A male subject age 72; the patient is Fitzpatrick phototype II; the chart notes tobacco use, pesticide exposure, and prior malignancy (patient or family); a smartphone photograph of a skin lesion: 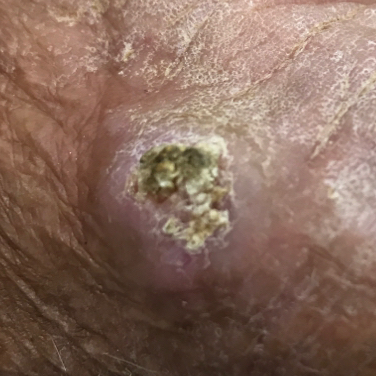Findings:
The lesion was found on a hand. By the patient's account, the lesion itches, is elevated, has bled, and hurts.
Conclusion:
On biopsy, the diagnosis was a malignancy — a squamous cell carcinoma.